A dermoscopic photograph of a skin lesion.
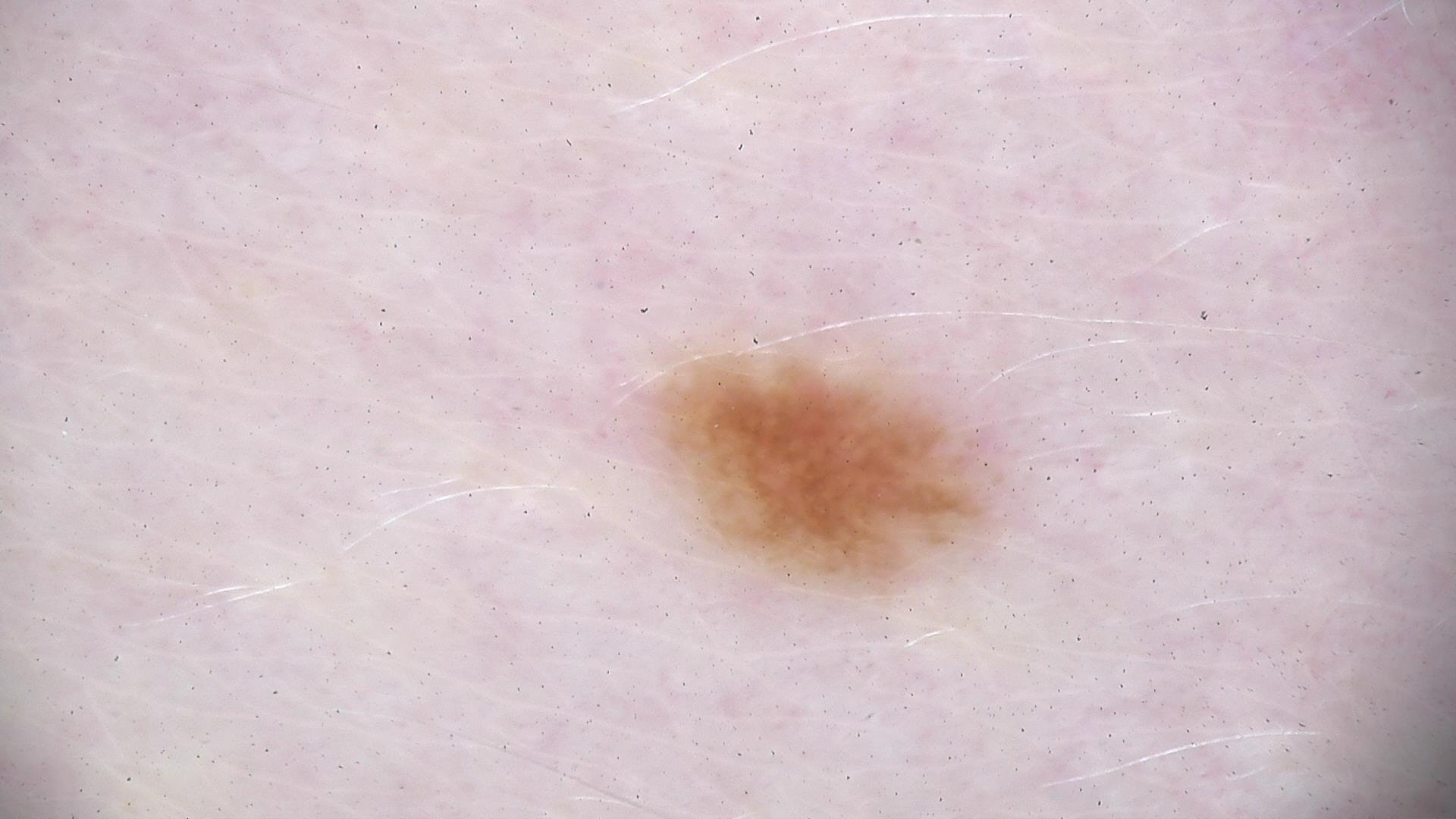assessment=dysplastic junctional nevus (expert consensus).